The arm is involved, an image taken at an angle, the subject is male.
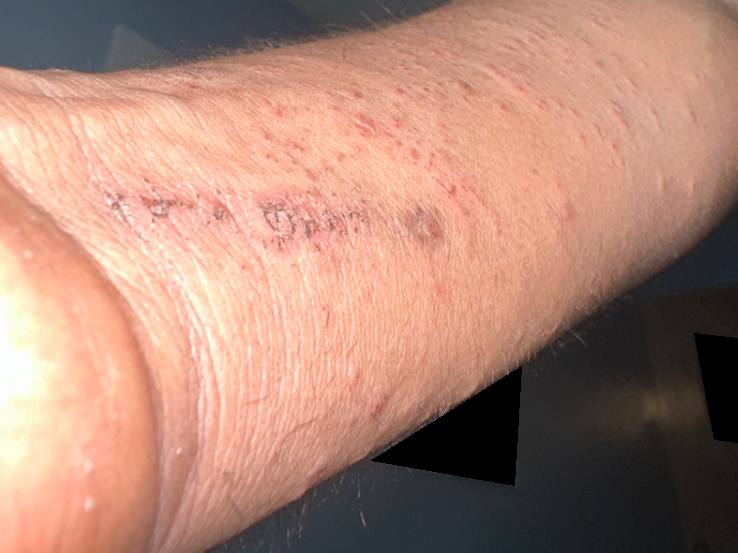On remote dermatologist review: the leading consideration is Eczema; the differential also includes Acute dermatitis, NOS; also consider Allergic Contact Dermatitis; less likely is Lichen planus/lichenoid eruption.